Contact-polarized dermoscopy of a skin lesion — 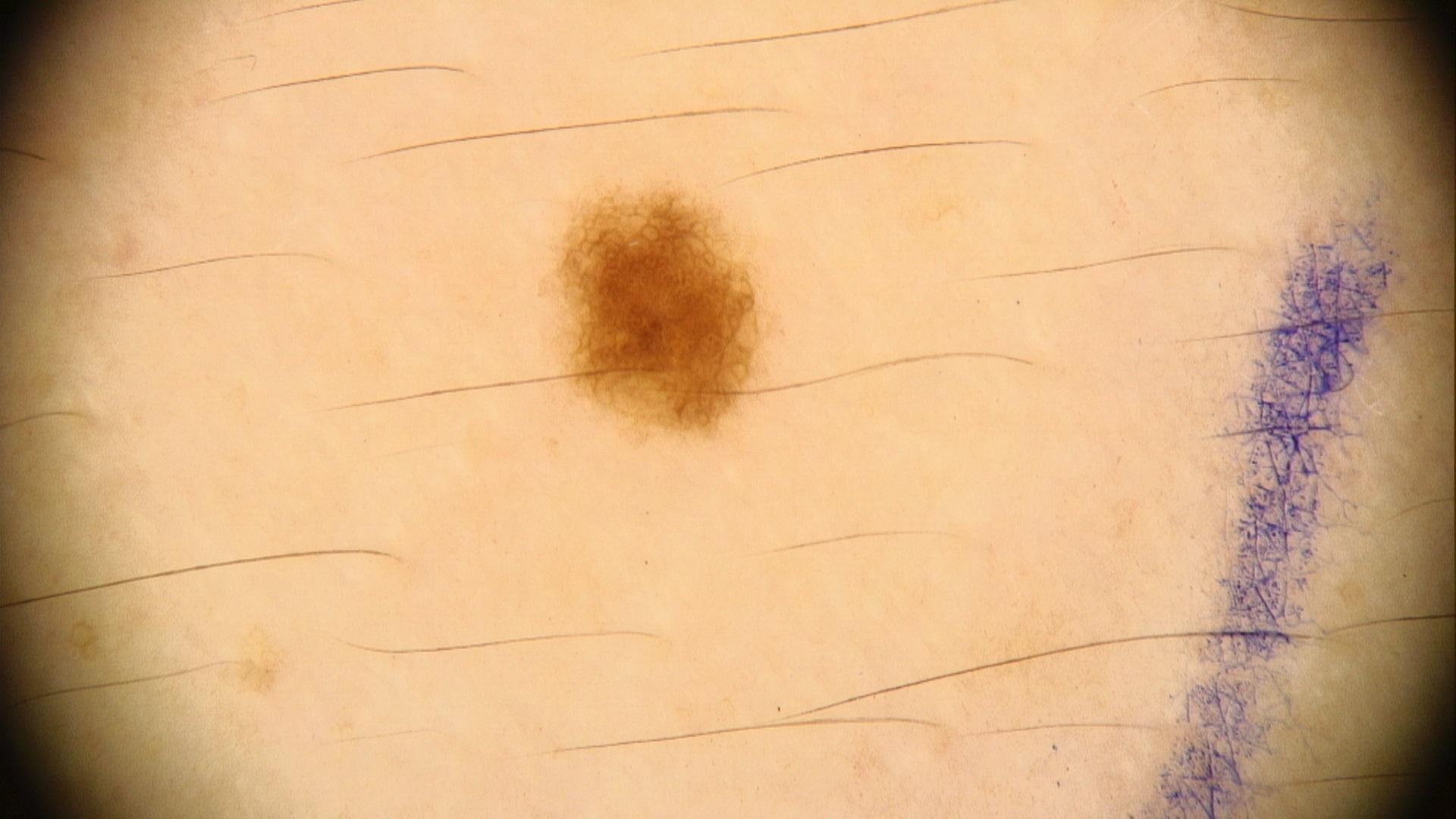The diagnostic impression was a benign, melanocytic lesion — a nevus.